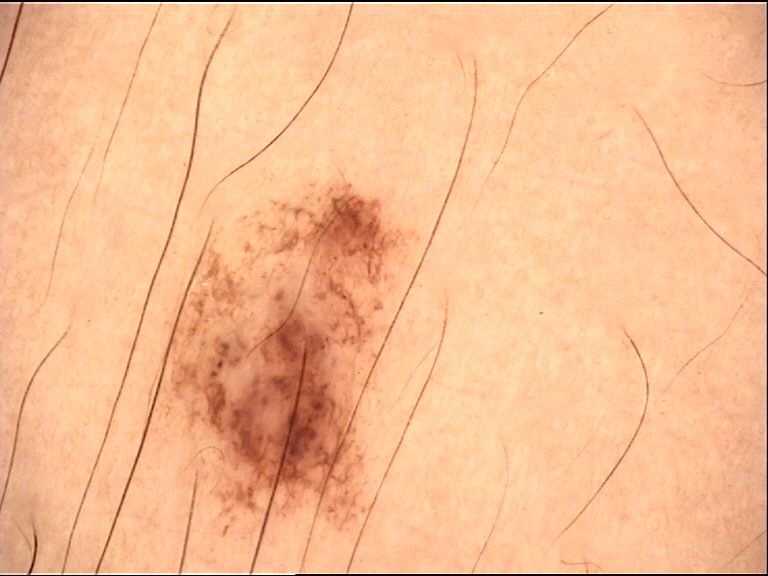Findings: A dermoscopic close-up of a skin lesion. Conclusion: Consistent with a dysplastic junctional nevus.